The patient says their skin reddens painfully with sun exposure · a female subject 35 years of age · acquired for a research image collection, with no referral diagnosis · a moderate number of moles by the patient's own estimate · dermoscopy of a skin lesion.
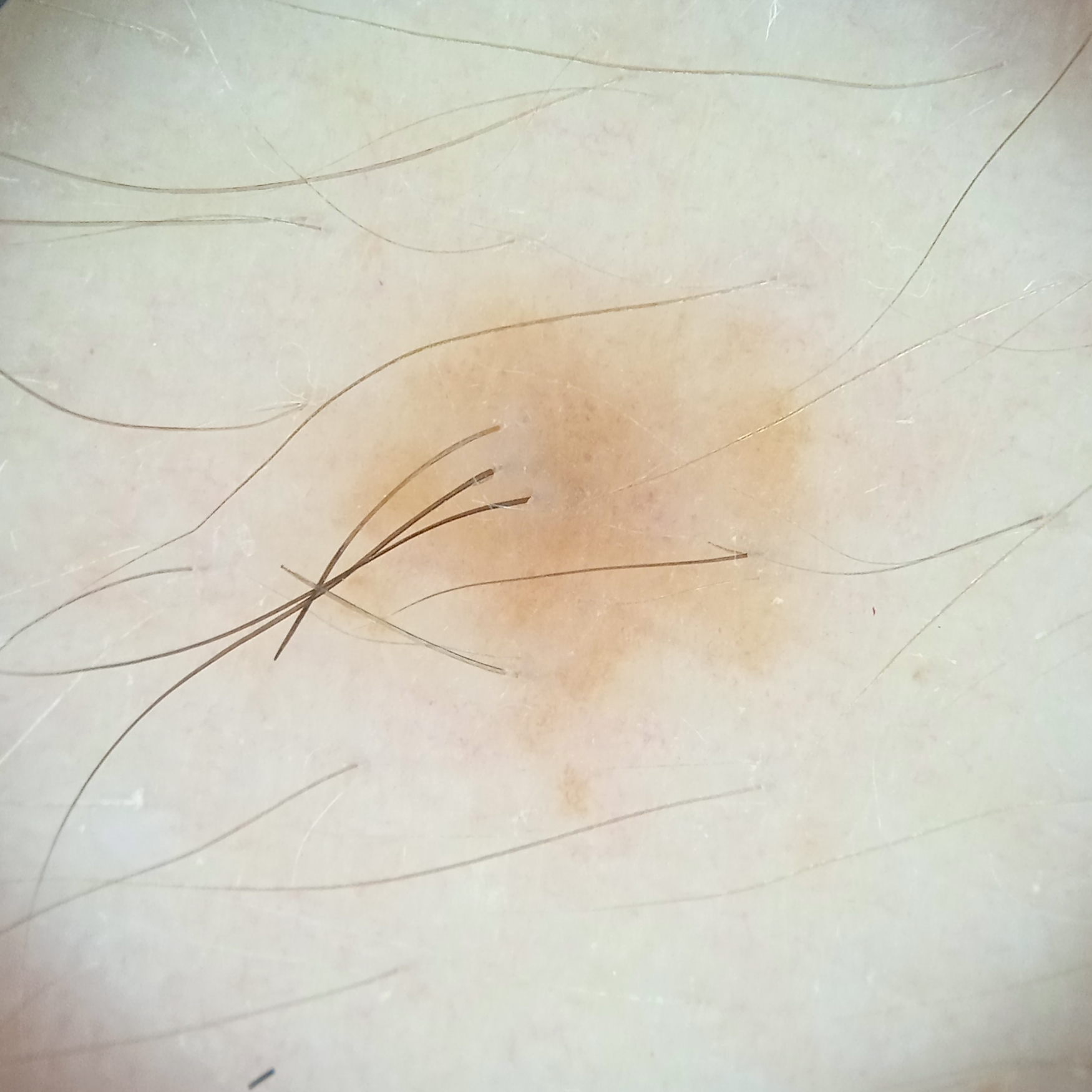Located on an arm. Measuring roughly 5.8 mm. The consensus diagnosis for this lesion was a melanocytic nevus.